A dermoscopy image of a single skin lesion.
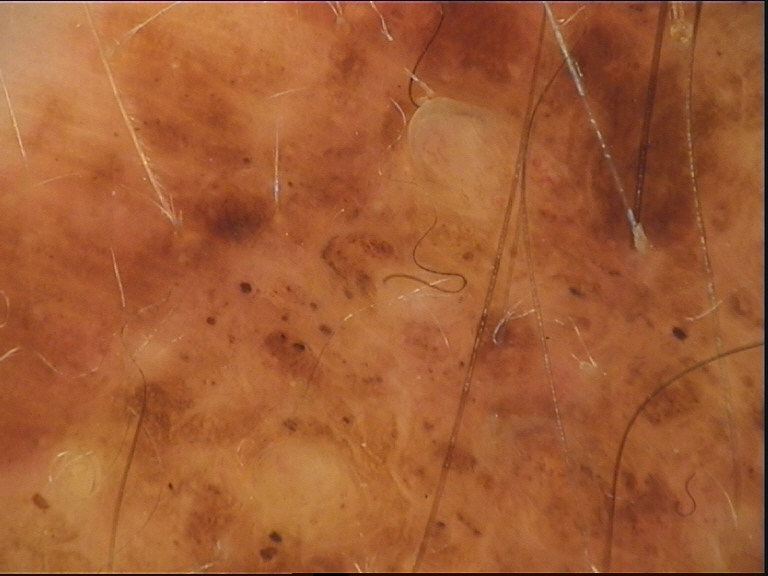diagnostic label: congenital compound nevus (expert consensus)